A skin lesion imaged with a dermatoscope; a female subject age 60; the patient reports a personal history of cancer and a personal history of skin cancer; the patient says their skin tans without first burning; referred for assessment of suspected basal cell carcinoma; few moles overall by the patient's own estimate — 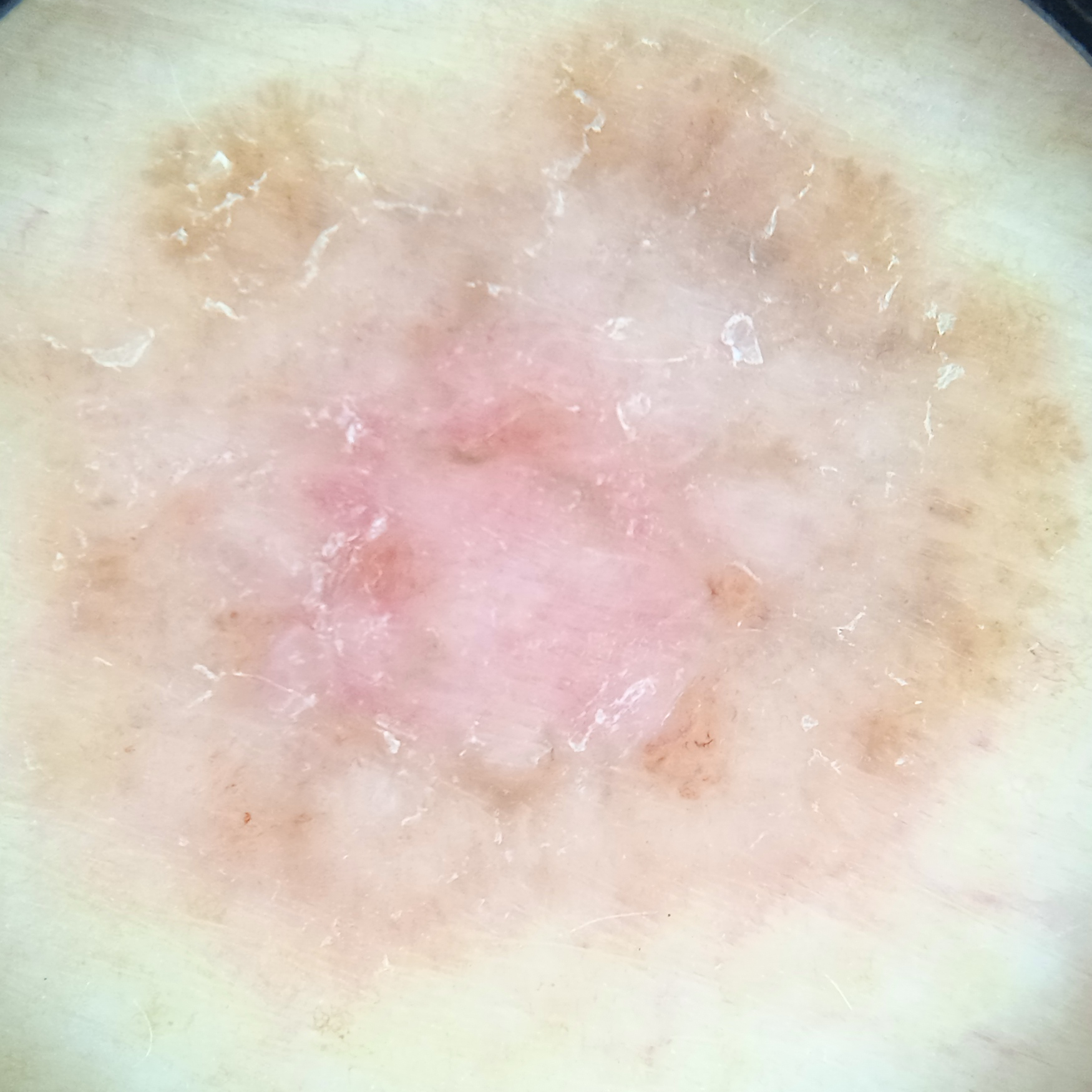Findings:
Located on the torso. Measuring roughly 13.2 mm.
Conclusion:
Dermatologist review favored a basal cell carcinoma.